The patient reports no family history of skin cancer; a moderate number of moles by the patient's own estimate; the patient says their skin tans without first burning; a male patient age 72; acquired for a research image collection, with no referral diagnosis; a clinical photograph of a skin lesion — 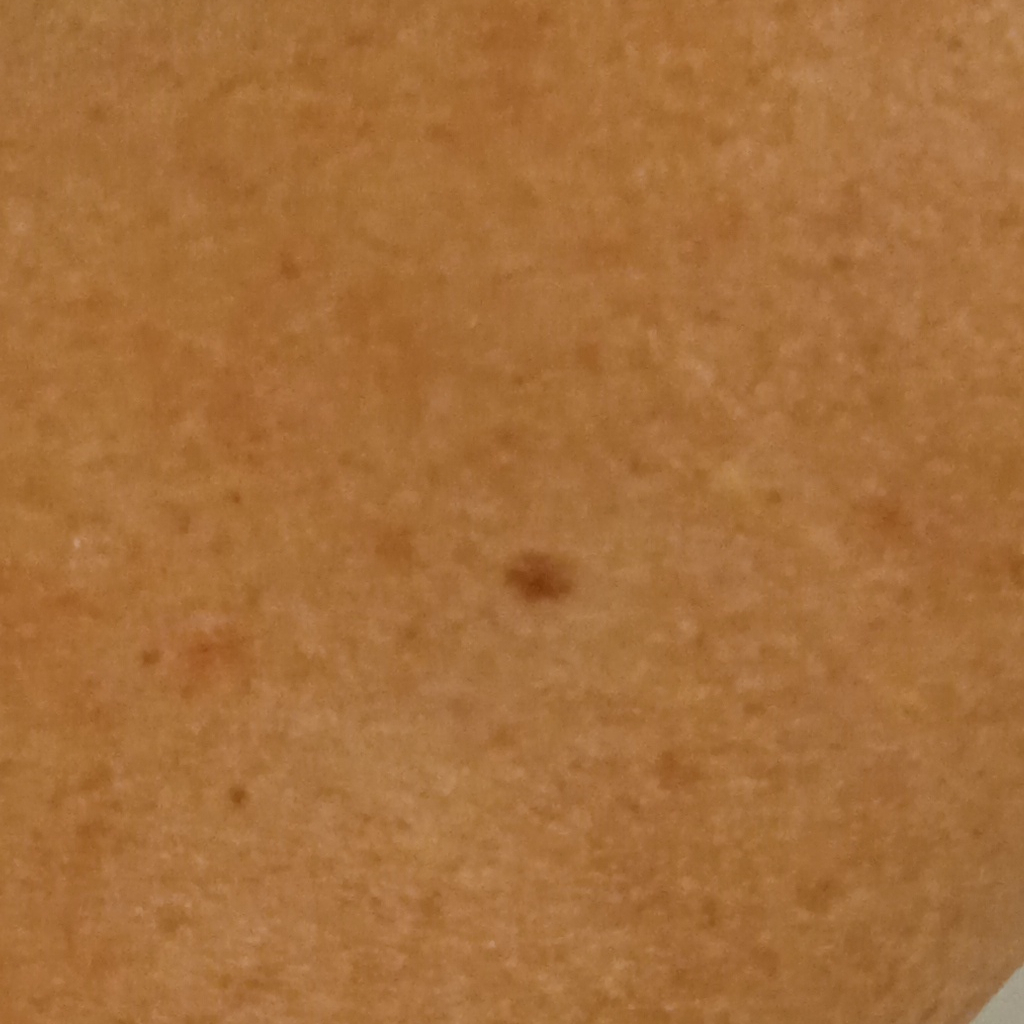site: the back | assessment: melanocytic nevus (dermatologist consensus).